The photo was captured at an angle — 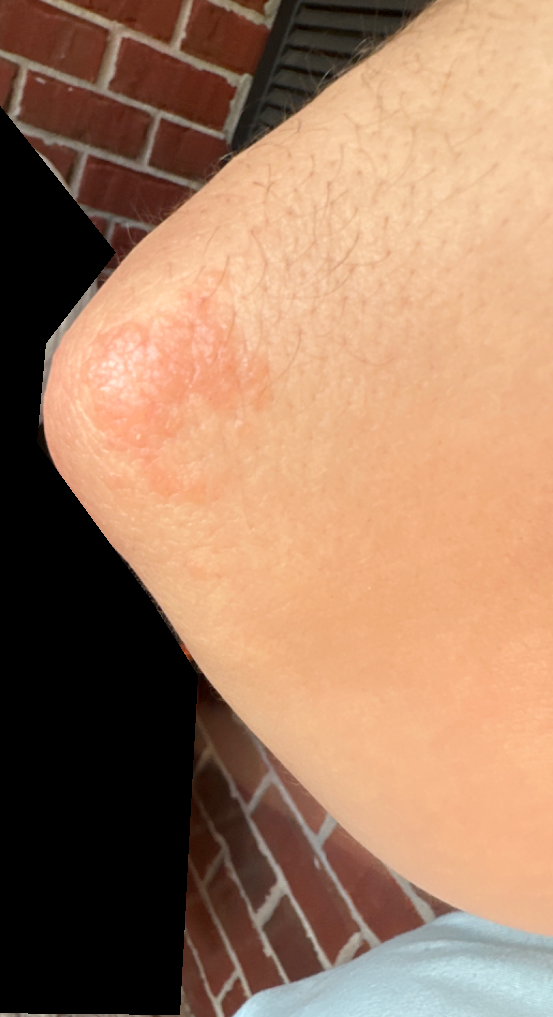The reviewing dermatologist was unable to assign a differential diagnosis from the image.